A skin lesion imaged with a dermatoscope:
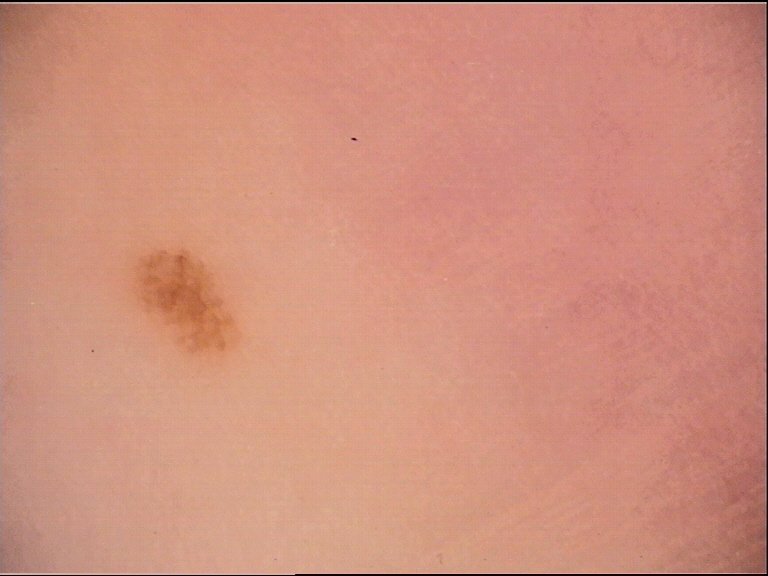– classification: banal
– diagnostic label: junctional nevus (expert consensus)